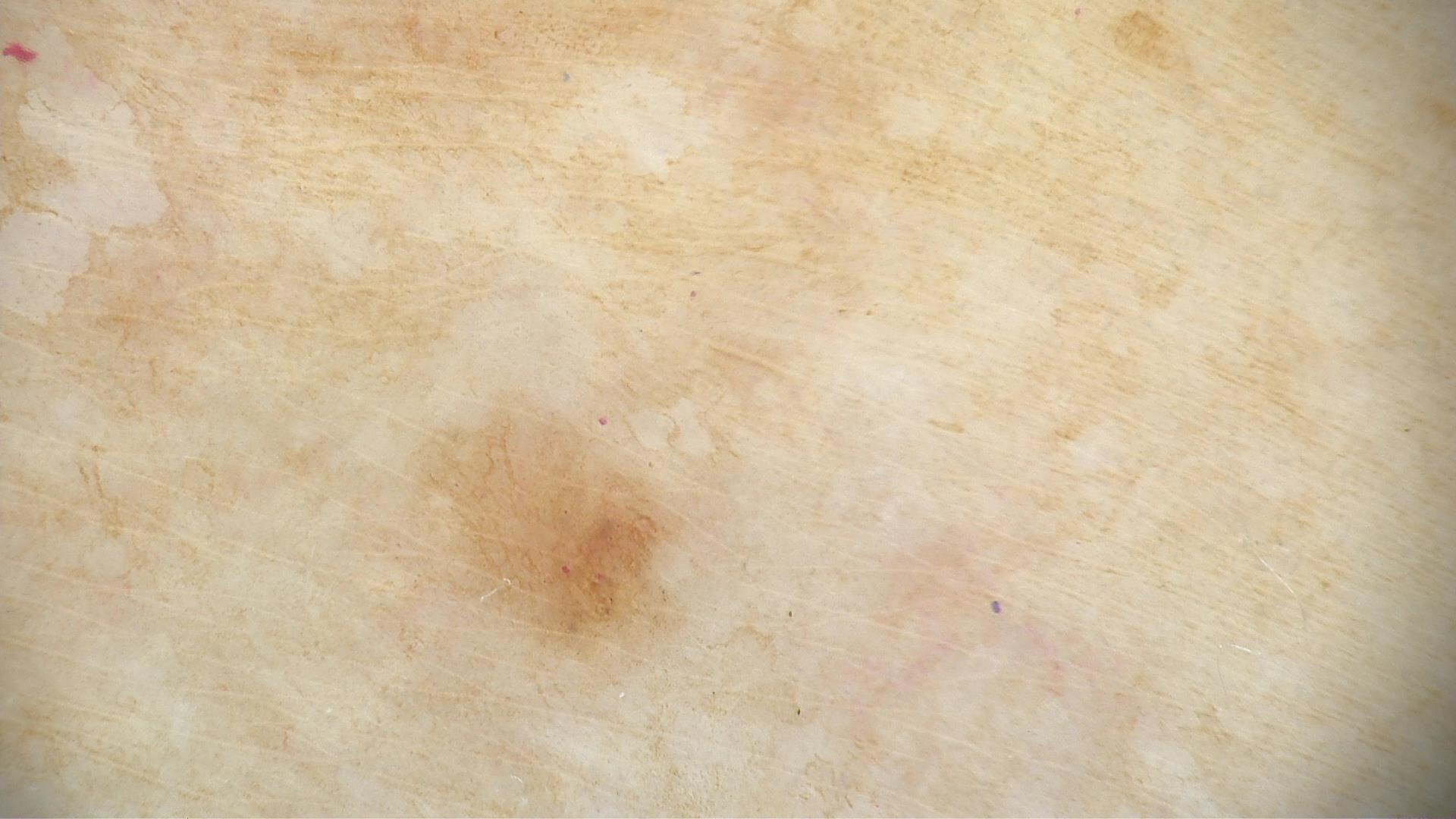{"diagnosis": {"name": "junctional nevus", "code": "jb", "malignancy": "benign", "super_class": "melanocytic", "confirmation": "expert consensus"}}